Dermoscopy of a skin lesion:
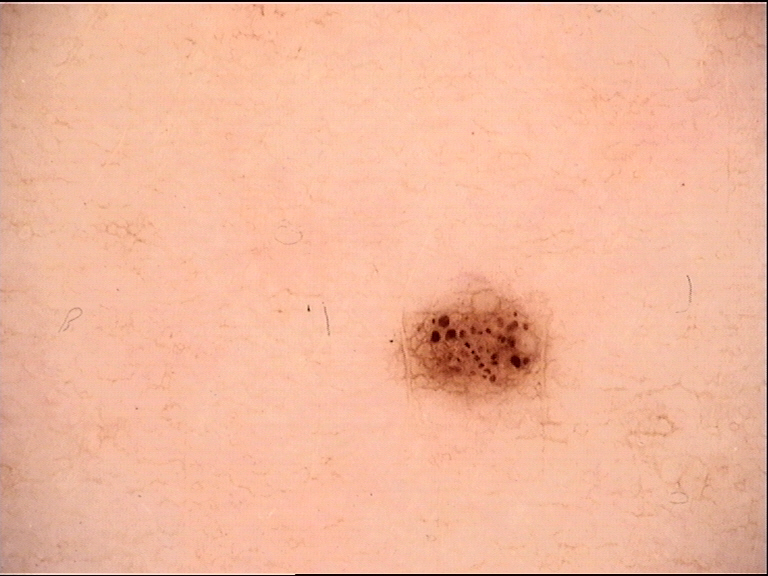Q: What is the diagnosis?
A: dysplastic junctional nevus (expert consensus)